Dermoscopy of a skin lesion.
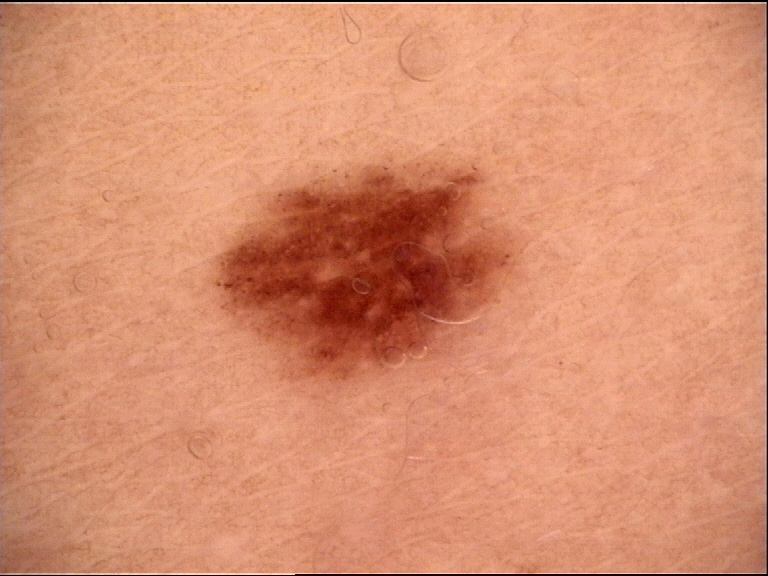class = dysplastic junctional nevus (expert consensus).